A clinical close-up photograph of a skin lesion; FST I: 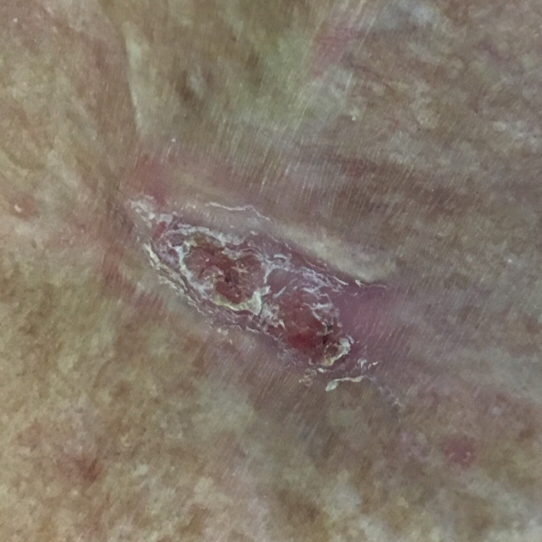The patient reports that the lesion has bled, is elevated, has grown, and itches. Histopathology confirmed a malignant lesion — a basal cell carcinoma.